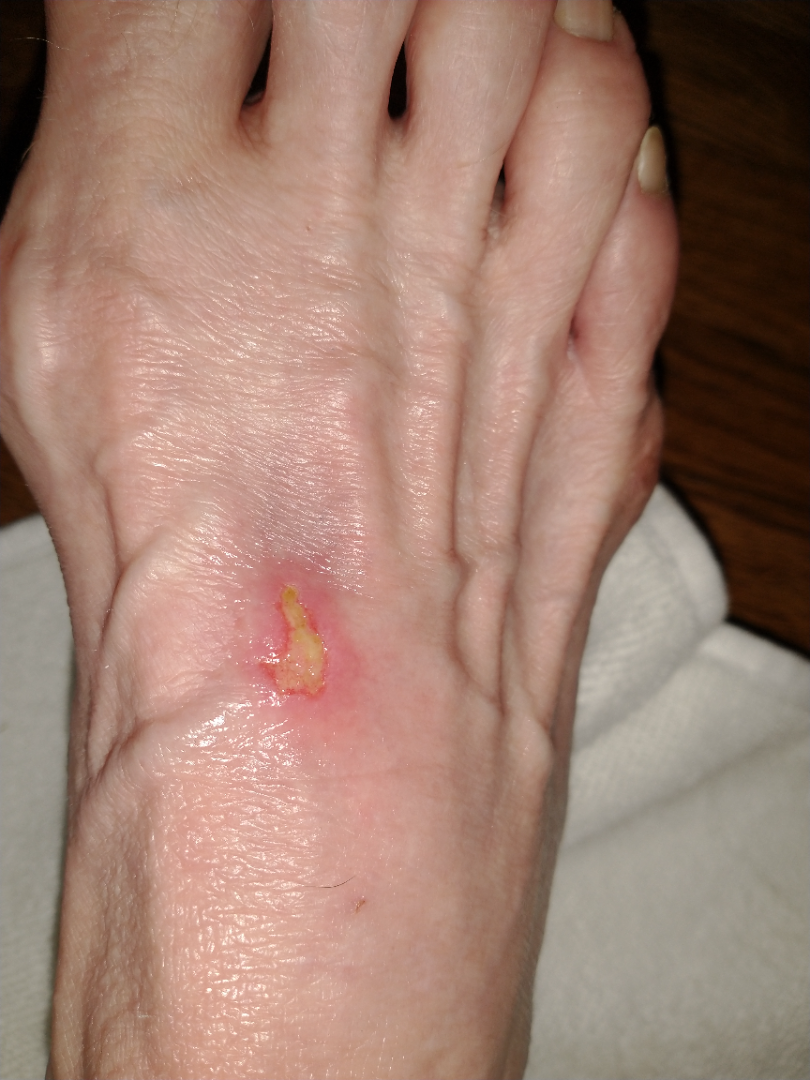Skin tone: Fitzpatrick phototype II. The patient notes the condition has been present for less than one week. Symptoms reported: bothersome appearance and burning. The affected area is the top or side of the foot. The photograph is a close-up of the affected area. On remote review of the image, consistent with Skin ulcer.